A female subject aged 27 · a moderate number of moles by the patient's own estimate · the patient says their skin reddens with sun exposure · imaged for a research study, with no referral diagnosis recorded · a dermoscopy image of a skin lesion: 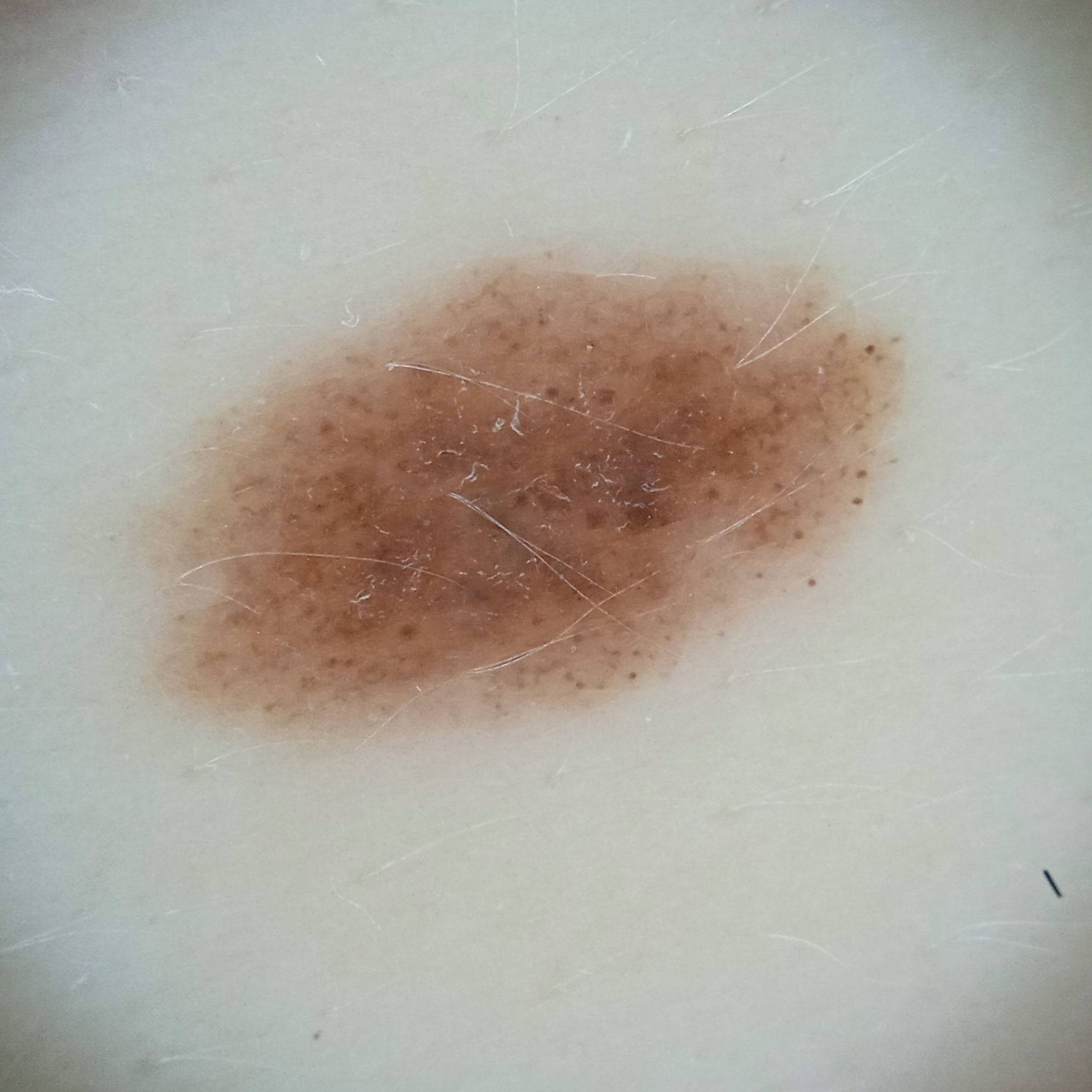{"lesion_location": "the back", "lesion_size": {"diameter_mm": 9.4}, "diagnosis": {"name": "melanocytic nevus", "malignancy": "benign"}}